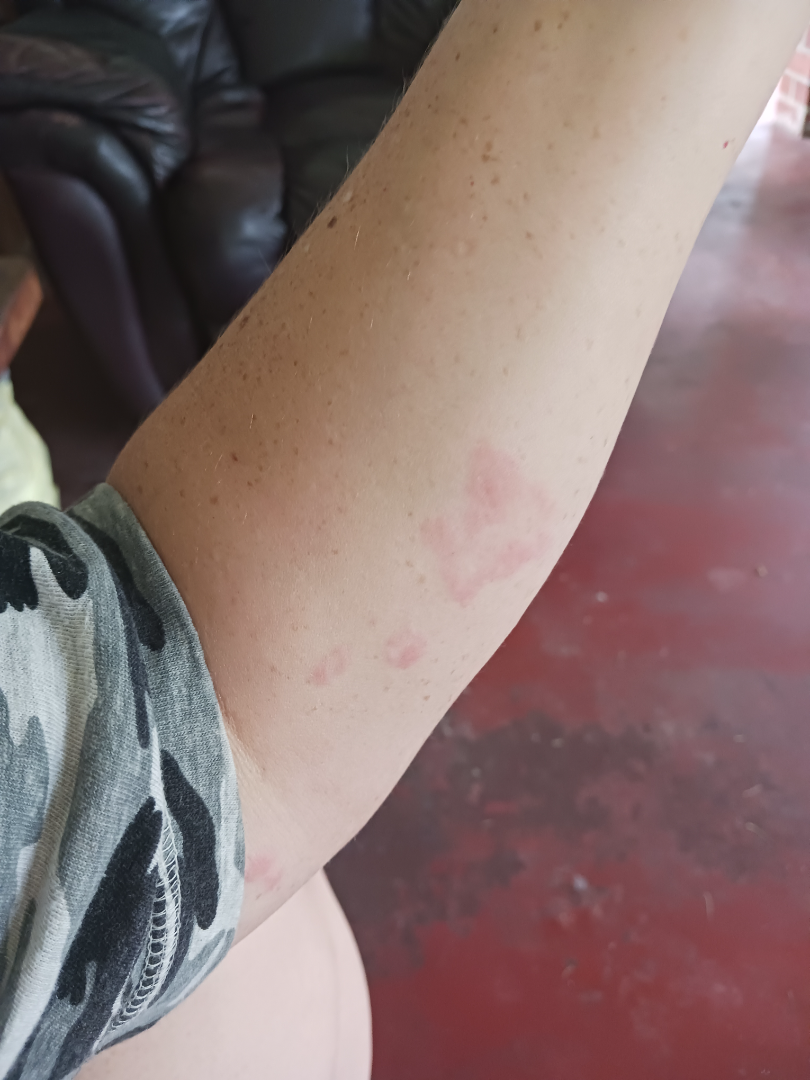Findings:
The case was difficult to assess from the available photograph.